Located on the back of the hand and arm · female patient, age 18–29 · this image was taken at an angle — 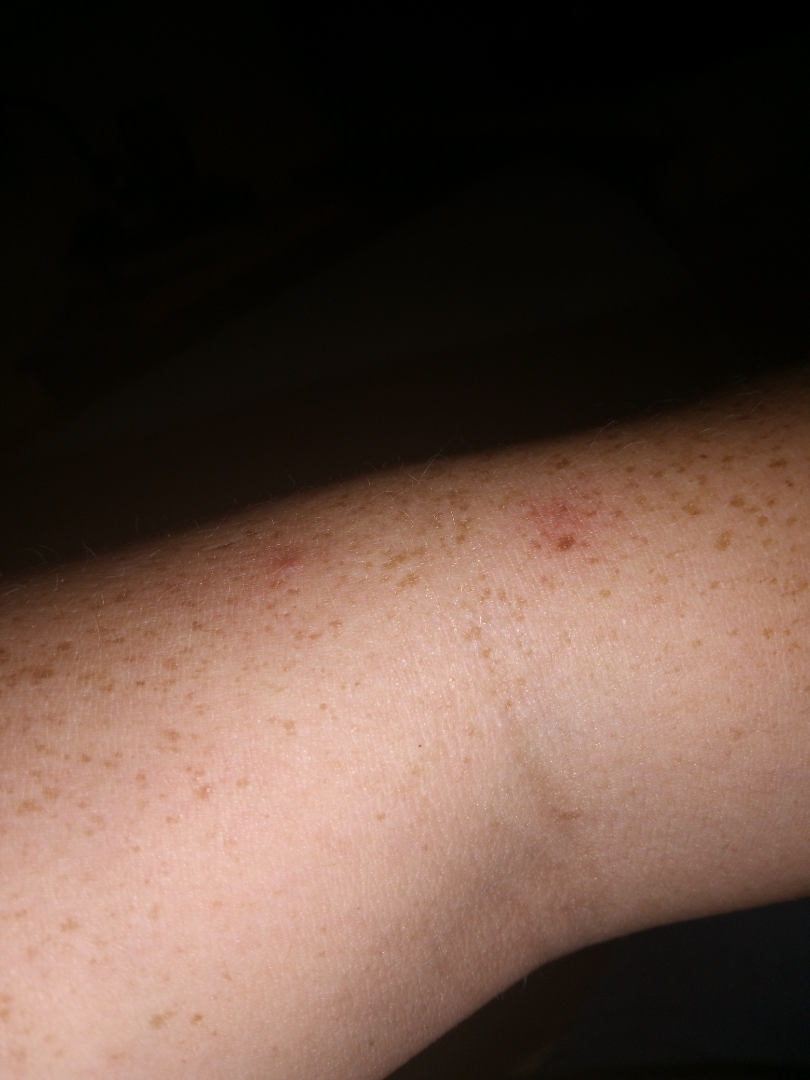Reported duration is more than one year.
Skin tone: Fitzpatrick skin type III; non-clinician graders estimated MST 3.
Texture is reported as raised or bumpy and flat.
No constitutional symptoms were reported.
The reviewing clinician's impression was: the differential includes Folliculitis and Insect Bite, with no clear leading consideration.